The contributor notes associated fatigue; reported lesion symptoms include itching and bothersome appearance; self-categorized by the patient as a rash; texture is reported as raised or bumpy; the patient is a male aged 18–29; the photograph is a close-up of the affected area; located on the arm and leg:
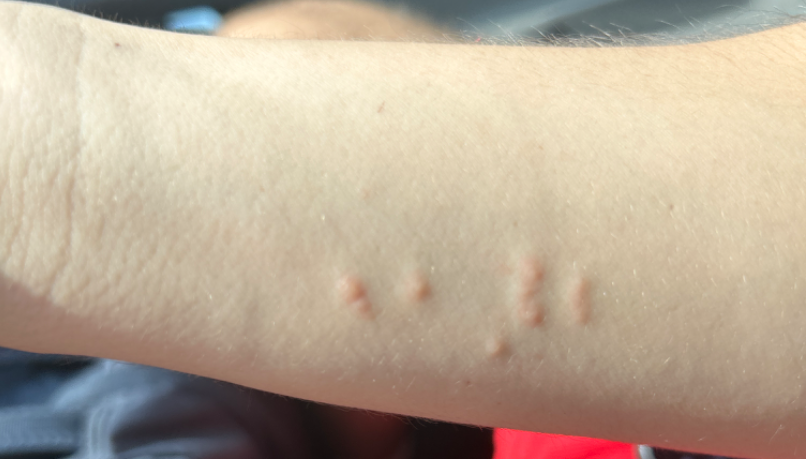Q: What was the assessment?
A: not assessable